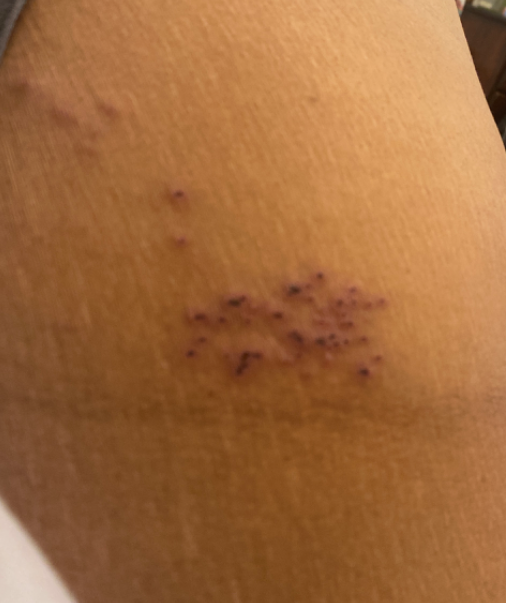Q: Where on the body?
A: back of the torso and front of the torso
Q: Patient demographics?
A: male, age 30–39
Q: How was the photo taken?
A: at an angle
Q: What is the dermatologist's impression?
A: most consistent with Herpes Simplex; also raised was Herpes Zoster; possibly Lymphangioma; less probable is Dermatitis herpetiformis